A skin lesion imaged with a dermatoscope:
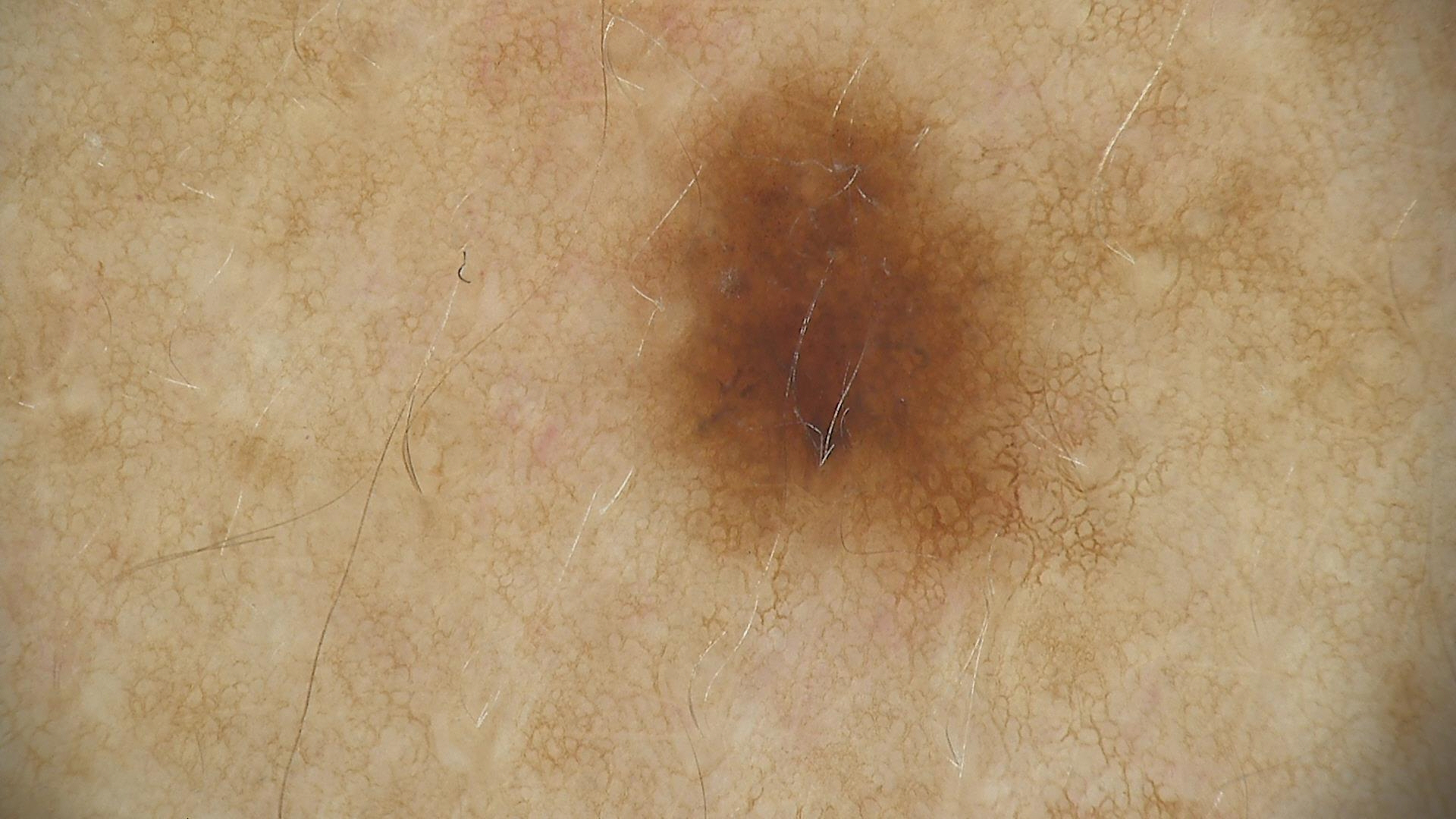assessment — dysplastic junctional nevus (expert consensus).